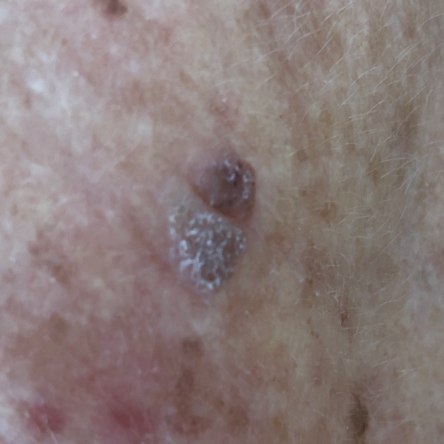subject = in their late 70s | region = the face | reported symptoms = elevation | impression = seborrheic keratosis (clinical consensus).